A male subject, aged around 25 · a dermoscopic image of a skin lesion: 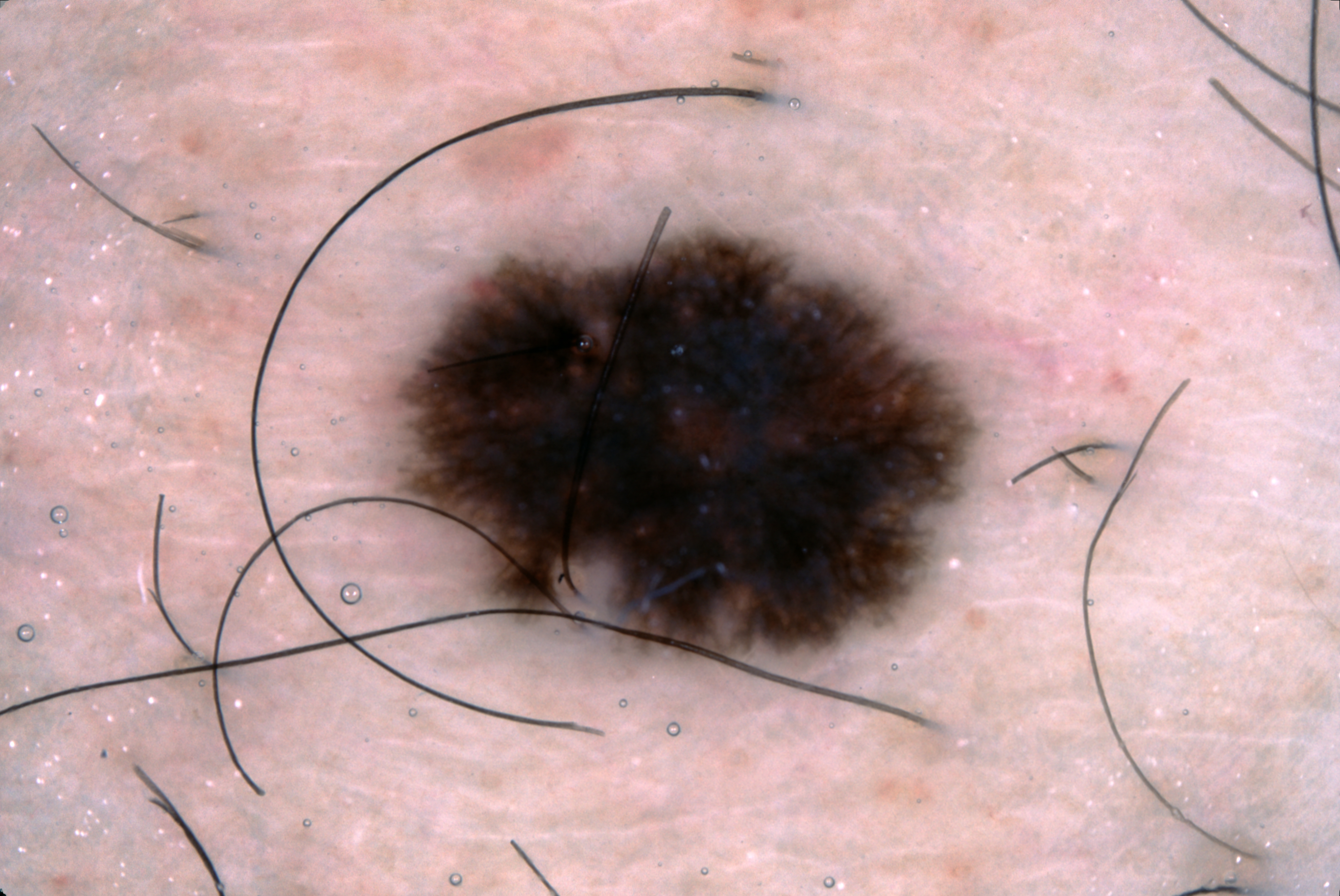<record>
<dermoscopic_features>
  <present>pigment network</present>
  <absent>negative network, streaks, milia-like cysts</absent>
</dermoscopic_features>
<lesion_location>
  <bbox_xyxy>370, 191, 994, 689</bbox_xyxy>
</lesion_location>
<lesion_extent>
  <approx_field_fraction_pct>21</approx_field_fraction_pct>
</lesion_extent>
<diagnosis>
  <name>melanocytic nevus</name>
  <malignancy>benign</malignancy>
  <lineage>melanocytic</lineage>
  <provenance>clinical</provenance>
</diagnosis>
</record>